The photo was captured at a distance, the arm is involved:
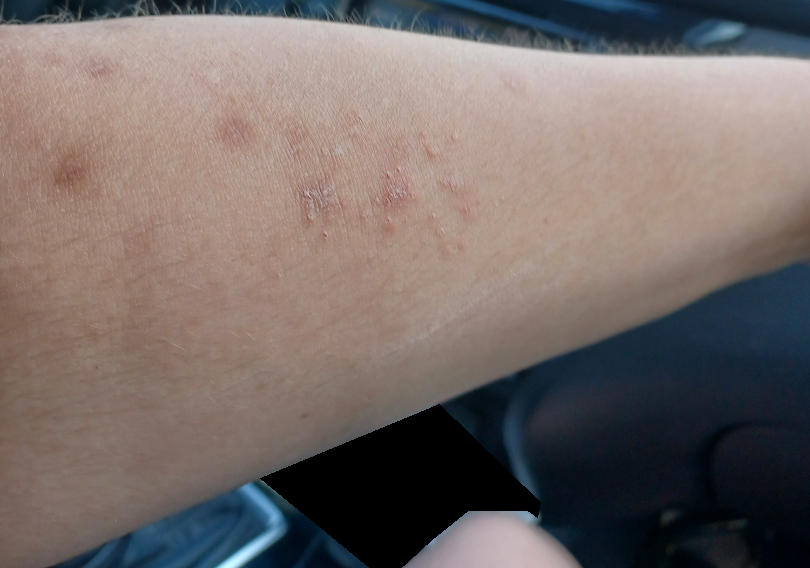{
  "systemic_symptoms": "fatigue",
  "texture": [
    "raised or bumpy",
    "rough or flaky"
  ],
  "patient_category": "a rash",
  "differential": {
    "Eczema": 0.3,
    "Allergic Contact Dermatitis": 0.3,
    "Chronic dermatitis, NOS": 0.21,
    "Herpes Zoster": 0.18
  }
}